A dermoscopic image of a skin lesion:
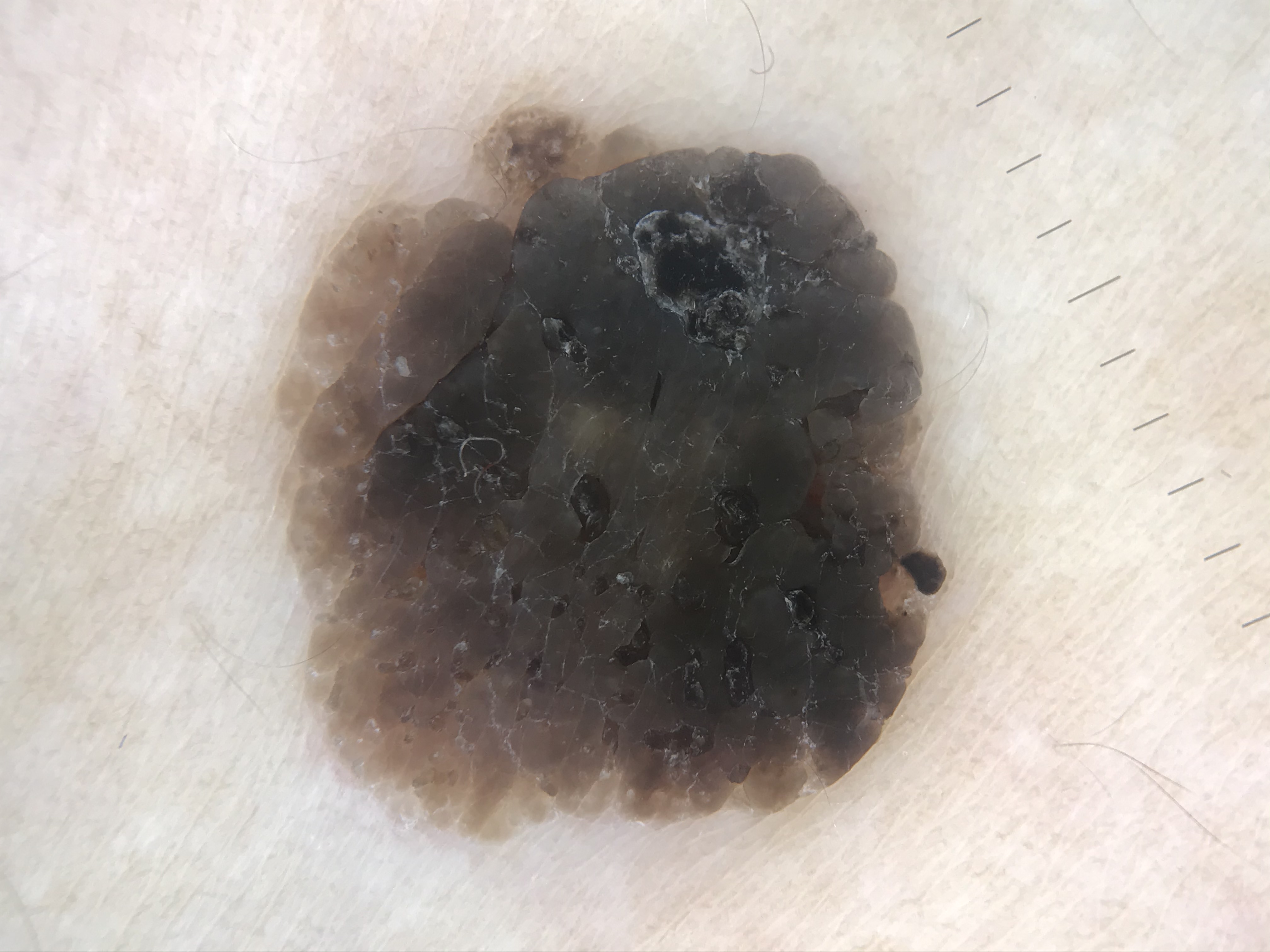Labeled as a keratinocytic lesion — a seborrheic keratosis.